This image was taken at a distance; the patient is 60–69, female: 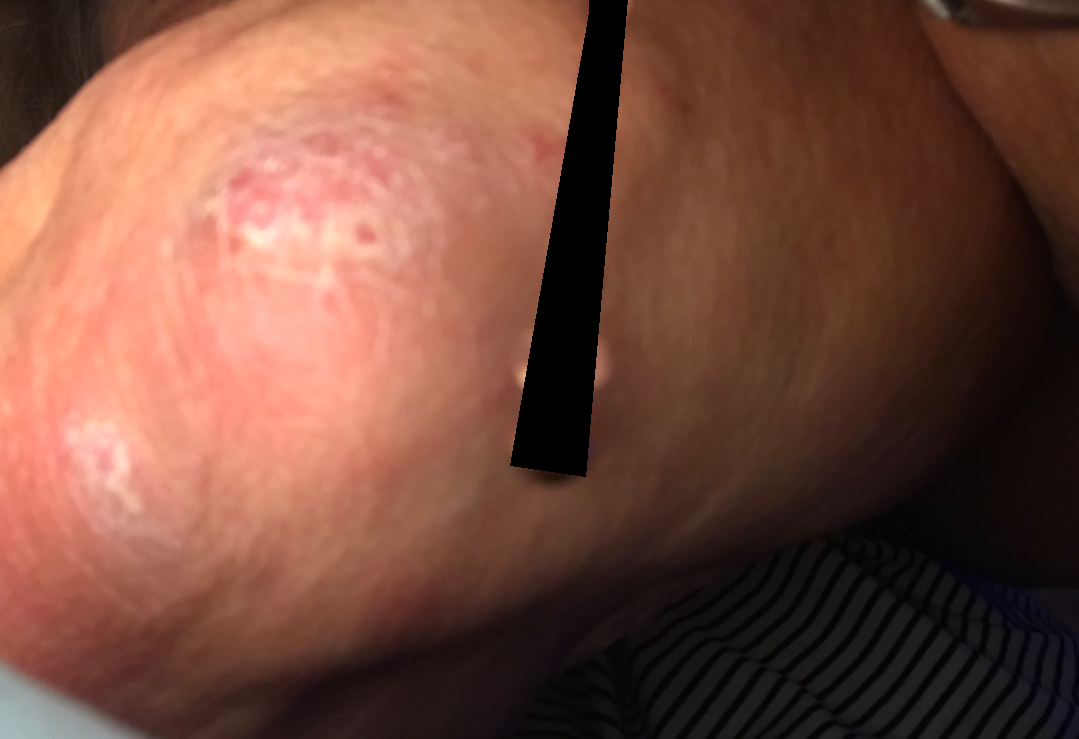Q: What conditions are considered?
A: the reviewer's impression was Psoriasis